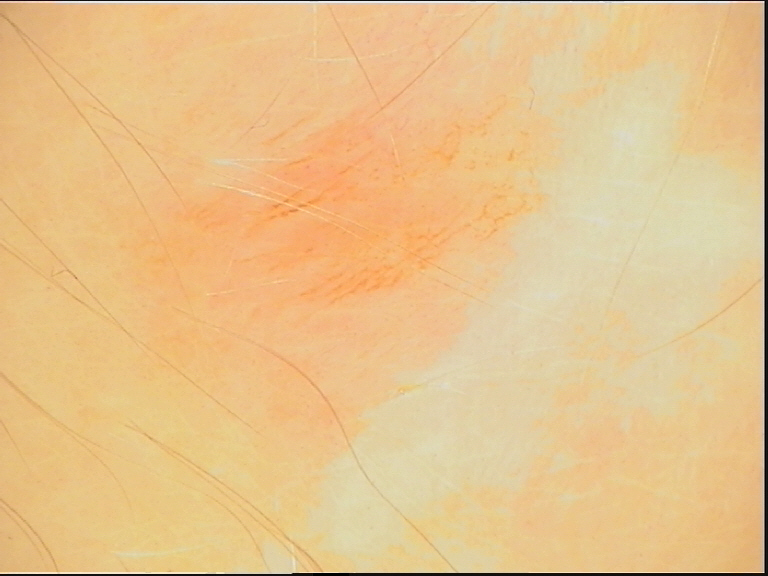diagnosis = acral dysplastic junctional nevus (expert consensus)